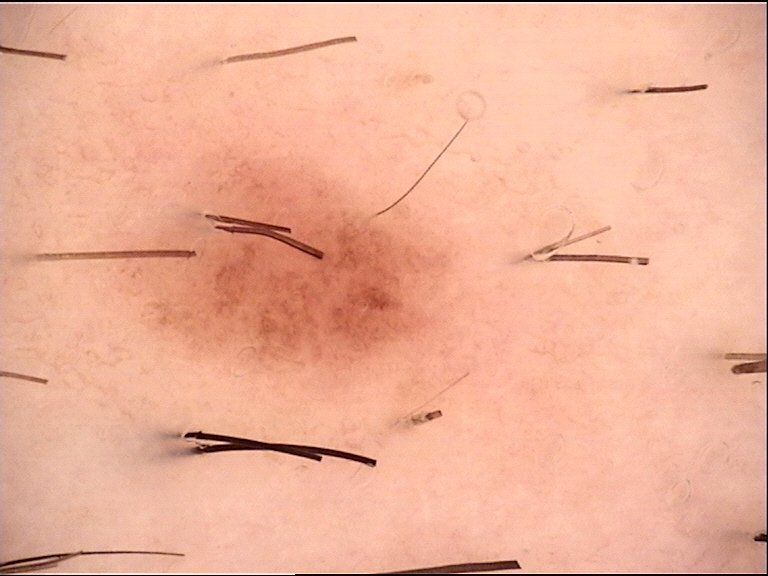{
  "diagnosis": {
    "name": "dysplastic junctional nevus",
    "code": "jd",
    "malignancy": "benign",
    "super_class": "melanocytic",
    "confirmation": "expert consensus"
  }
}